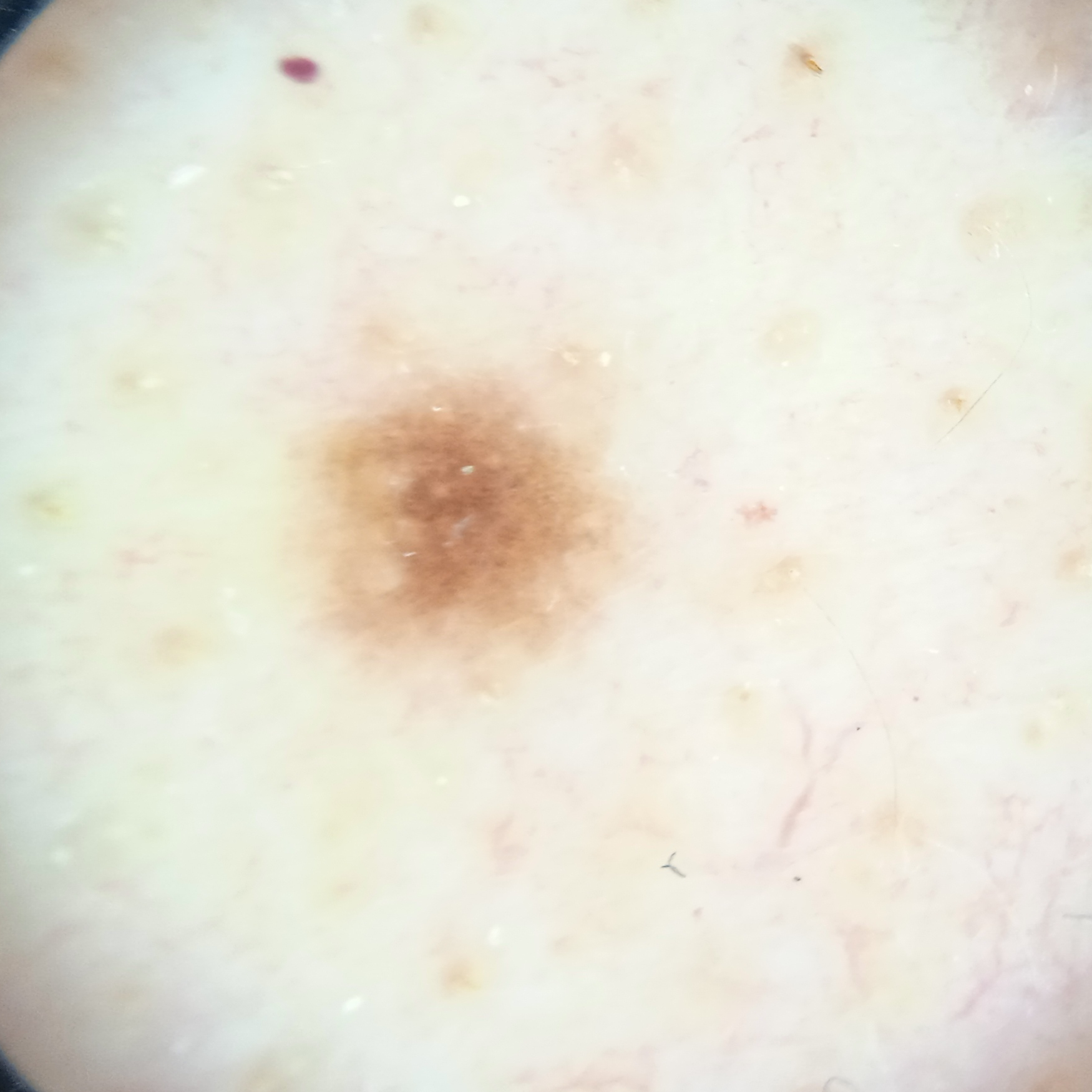A dermatoscopic image of a skin lesion. Imaged for a research study, with no referral diagnosis recorded. Numerous moles by the patient's own estimate. The patient says their skin reddens painfully with sun exposure. A male subject age 65. The lesion measures approximately 3.6 mm. The consensus diagnosis for this lesion was a melanocytic nevus.